This image was taken at a distance; located on the leg — 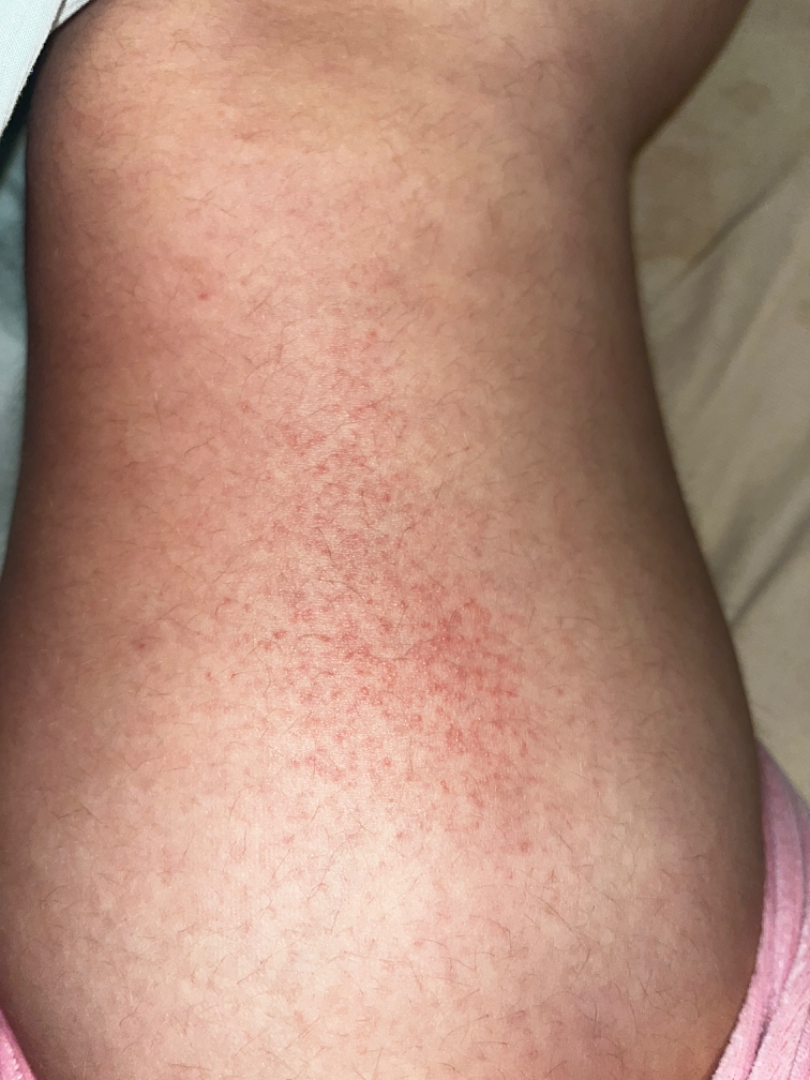{"differential": {"leading": ["Irritant Contact Dermatitis"], "considered": ["Eczema"]}}